Contact-polarized dermoscopy of a skin lesion · the patient was assessed as skin type III · a female patient aged approximately 45:
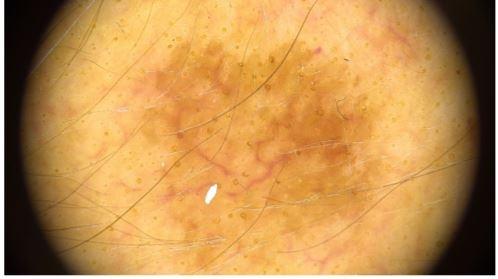The lesion involves the head or neck. Expert review favored an epidermal proliferation — a seborrheic keratosis.